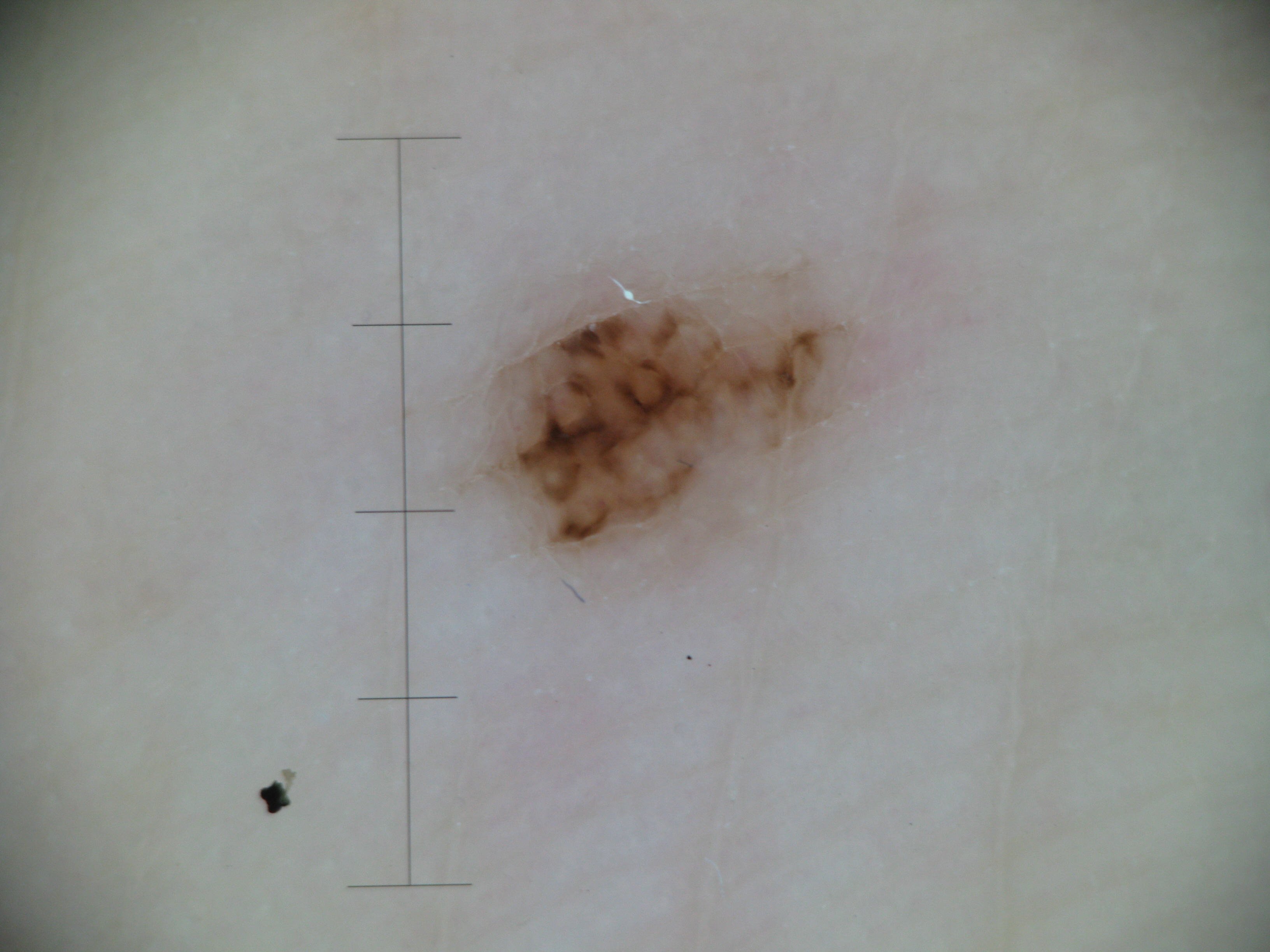A dermoscopic image of a skin lesion. This is a banal lesion. The diagnosis was an acral junctional nevus.